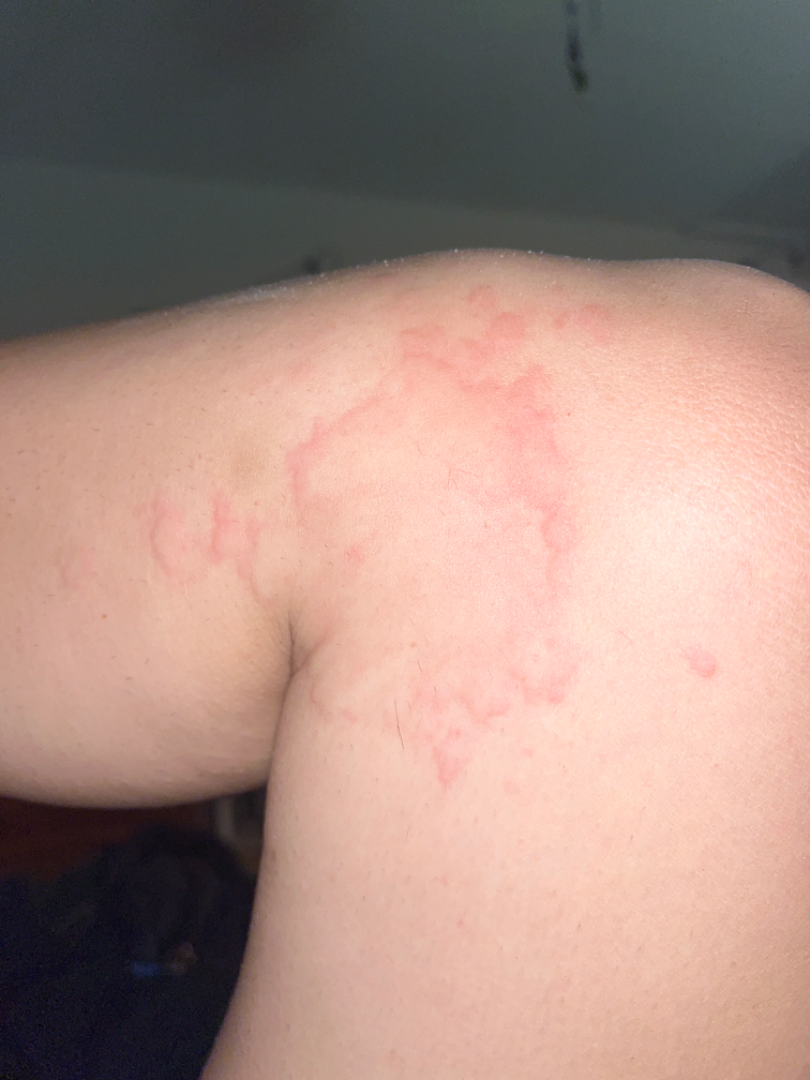{
  "differential": "Urticaria"
}